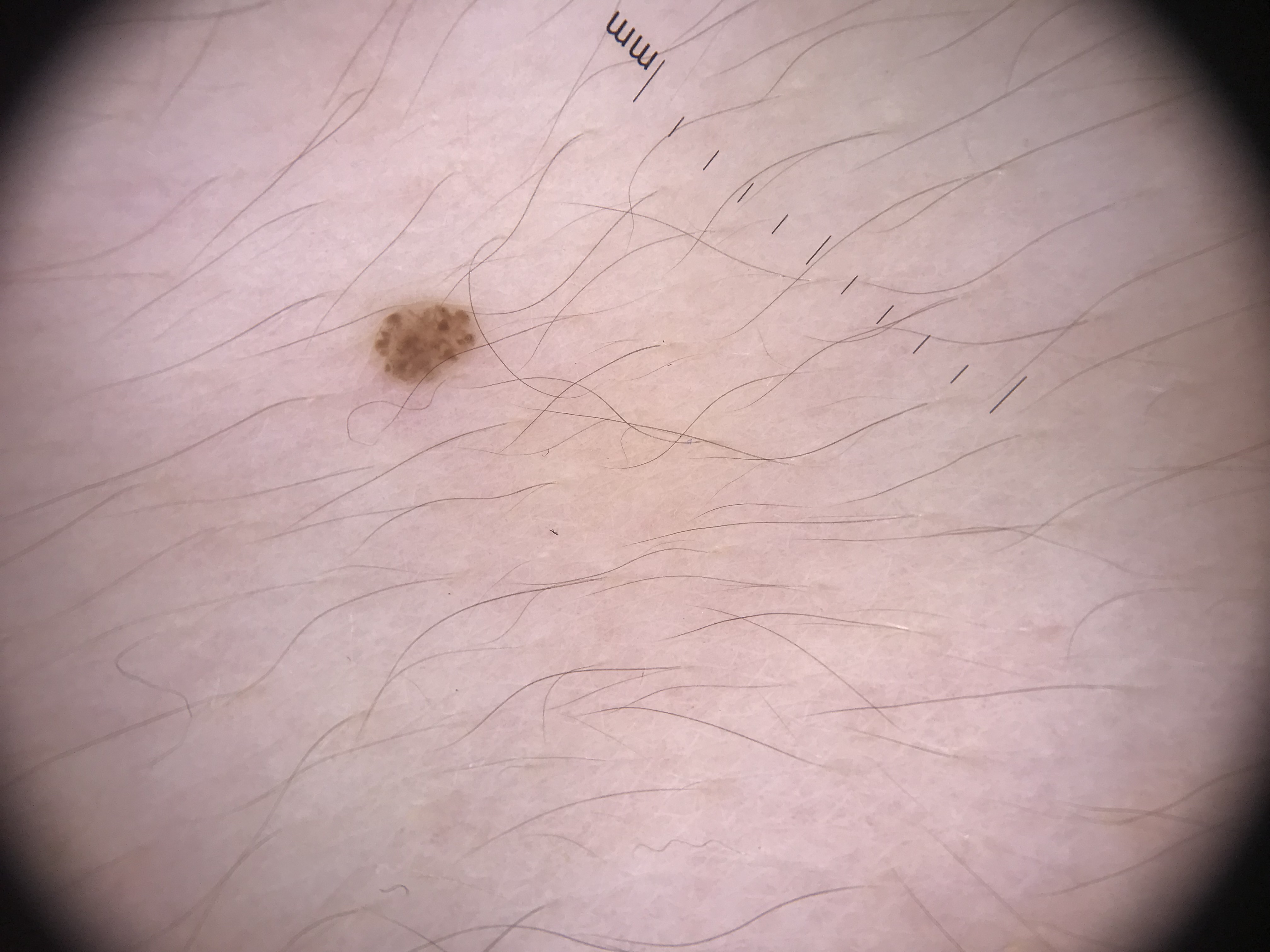Case:
A dermoscopic close-up of a skin lesion. The architecture is that of a banal lesion.
Conclusion:
Consistent with a junctional nevus.